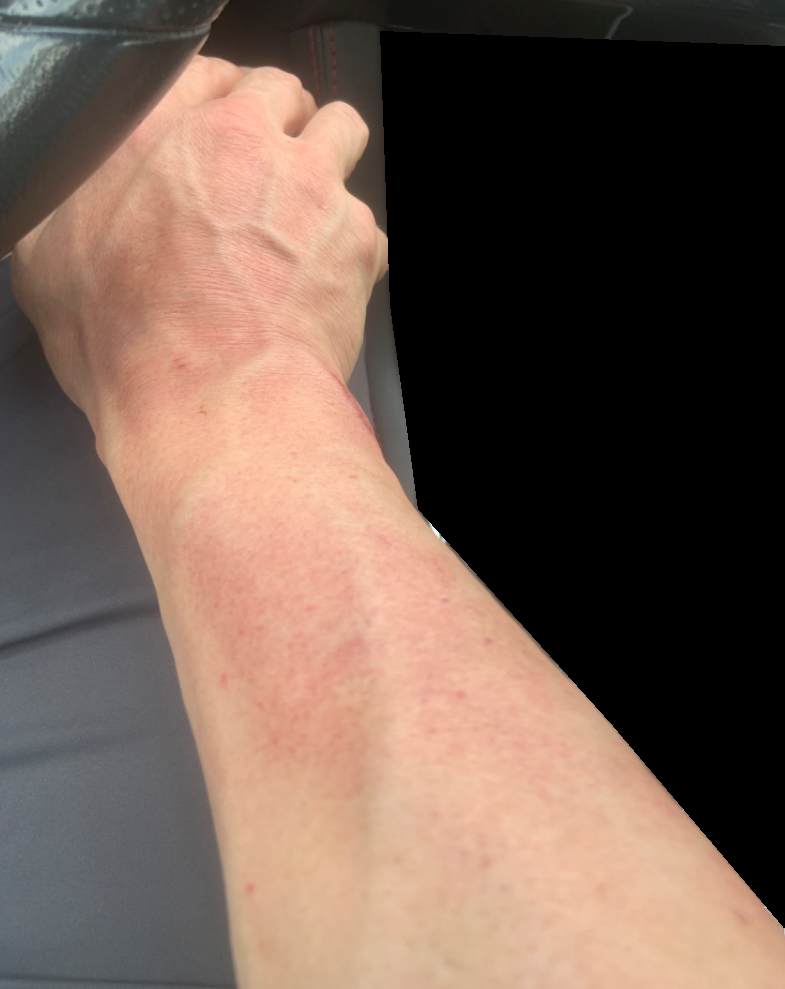Notes:
• assessment — indeterminate from the photograph
• affected area — arm
• patient — male, age 40–49
• self-categorized as — skin that appeared healthy to them
• present for — about one day
• surface texture — flat
• associated systemic symptoms — none reported
• reported symptoms — bothersome appearance
• shot type — close-up